This image was taken at a distance · located on the leg and front of the torso · the patient reported no systemic symptoms:
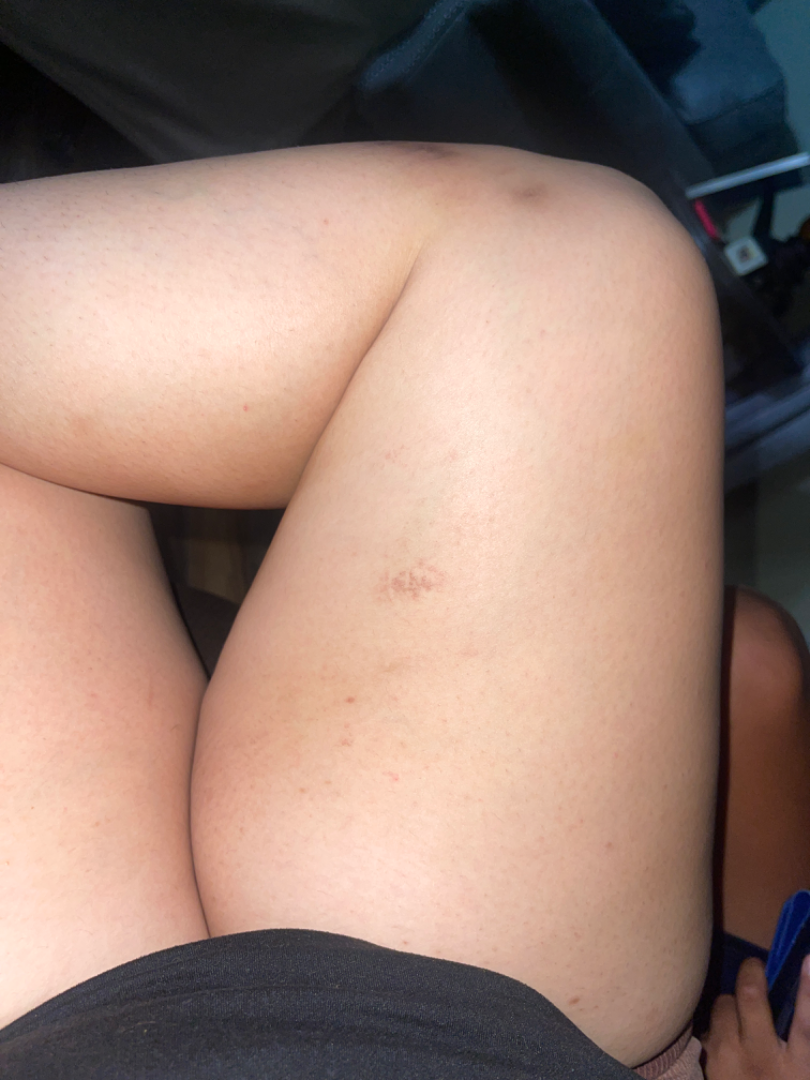{
  "differential": {
    "Eczema": 0.54,
    "Epidermal nevus": 0.23,
    "Milia": 0.23
  }
}